This is a close-up image:
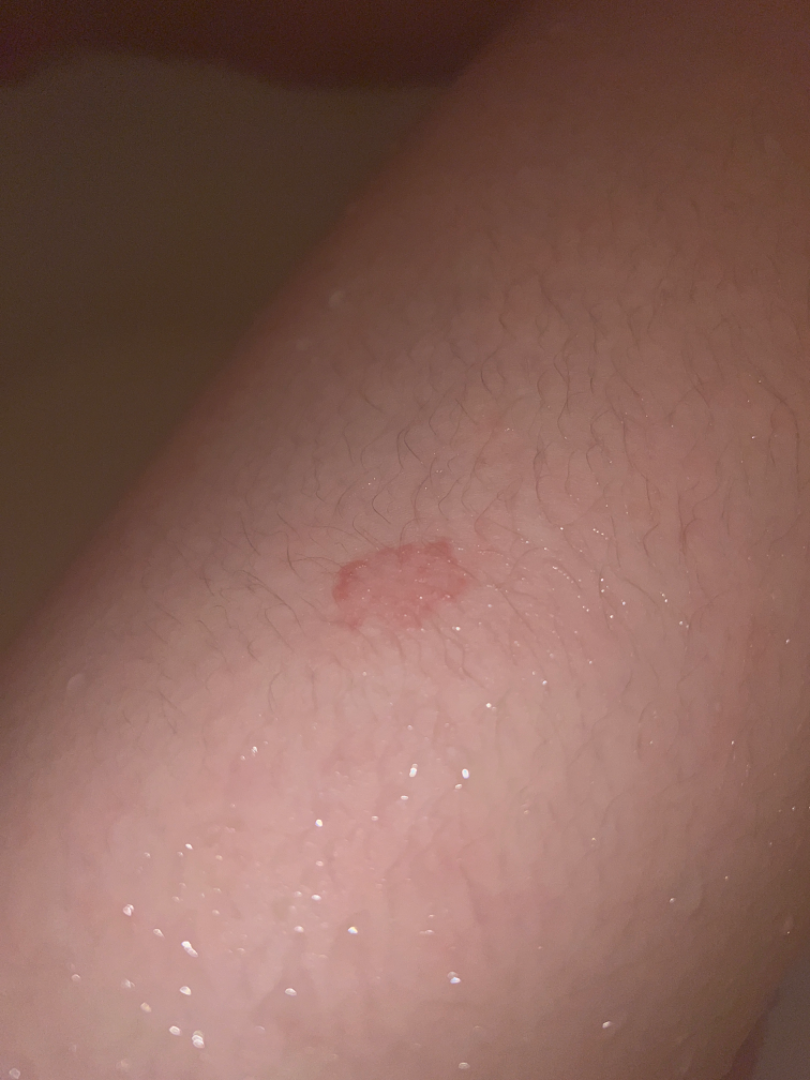dermatologist impression — reviewed remotely by one dermatologist: Tinea, Eczema and Pityriasis rosea were considered with similar weight.